The patient considered this a rash. The patient reported no systemic symptoms. Fitzpatrick V; non-clinician graders estimated Monk skin tone scale 7 or 8 (two reviewer pools). Symptoms reported: itching. The condition has been present for one to four weeks. The photograph is a close-up of the affected area. The lesion is described as rough or flaky and raised or bumpy. Located on the back of the hand. The subject is 18–29, male: 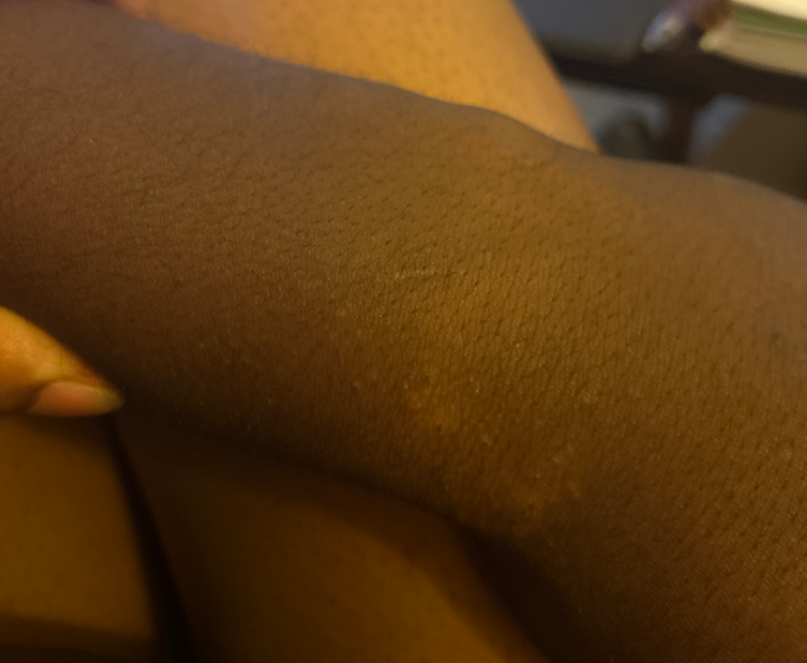On remote dermatologist review, Eczema (primary); Psoriasis (unlikely); Lichen planus/lichenoid eruption (unlikely).